A dermoscopic close-up of a skin lesion: 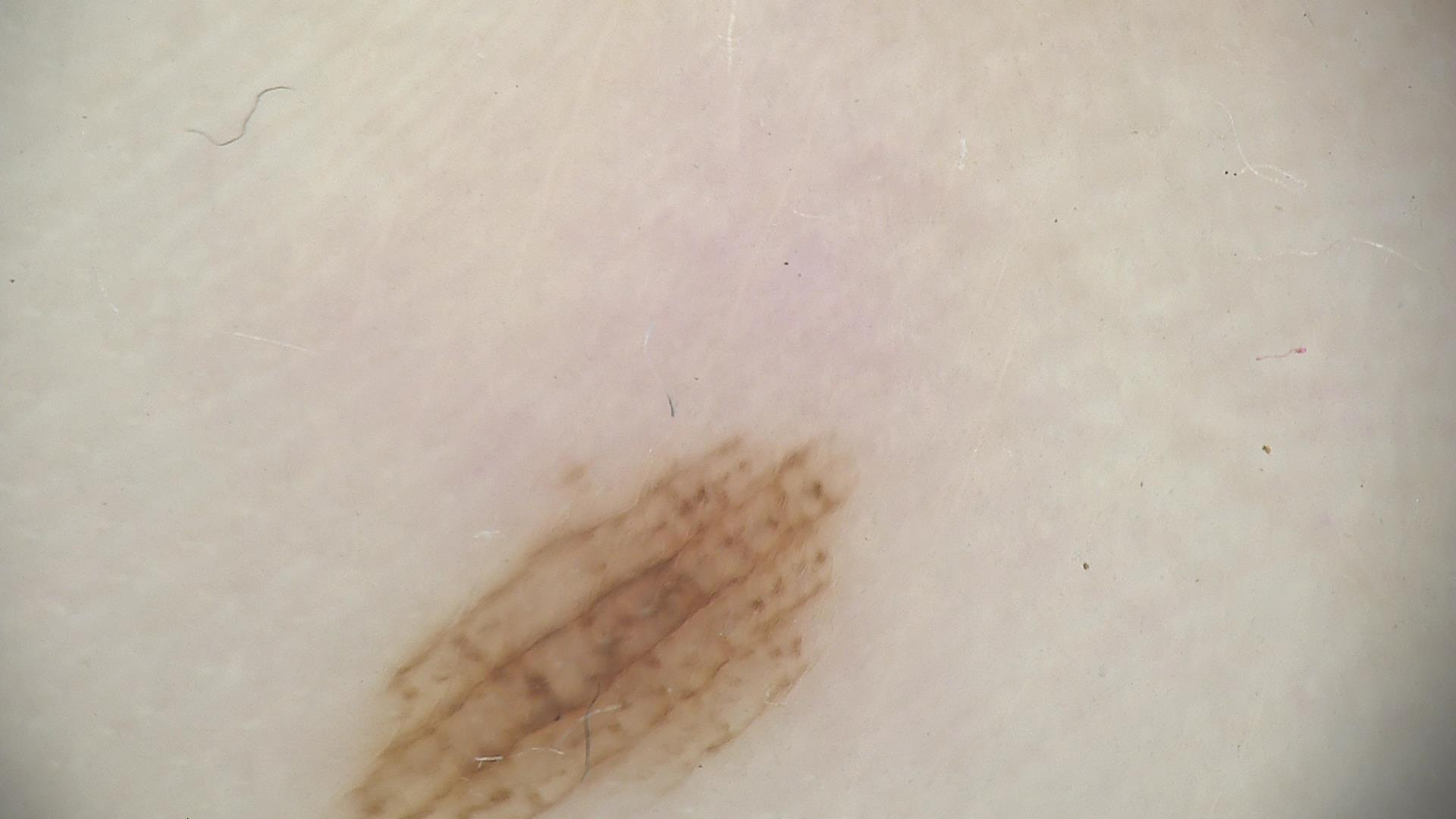{"diagnosis": {"name": "acral dysplastic junctional nevus", "code": "ajd", "malignancy": "benign", "super_class": "melanocytic", "confirmation": "expert consensus"}}